The subject is a female aged 50–59 · located on the arm · the condition has been present for about one day · the patient considered this a rash · close-up view: 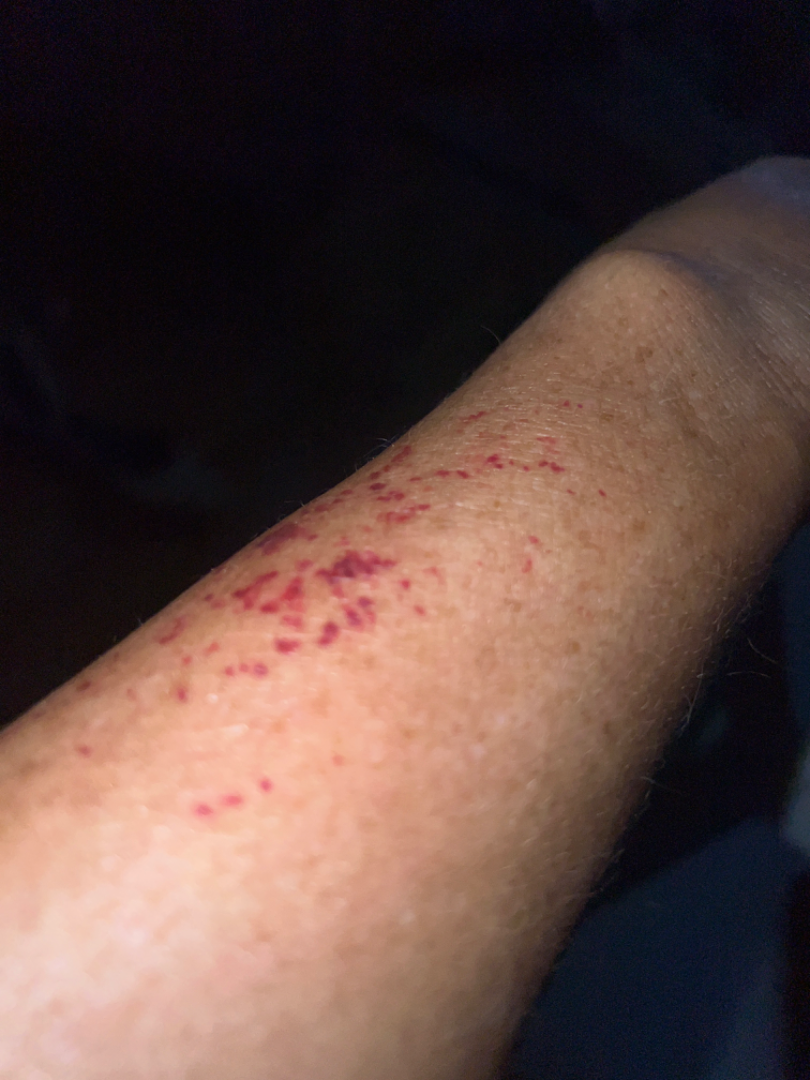Ecchymoses (leading); Purpura (possible); Leukocytoclastic Vasculitis (possible).